An image taken at a distance; the affected area is the head or neck:
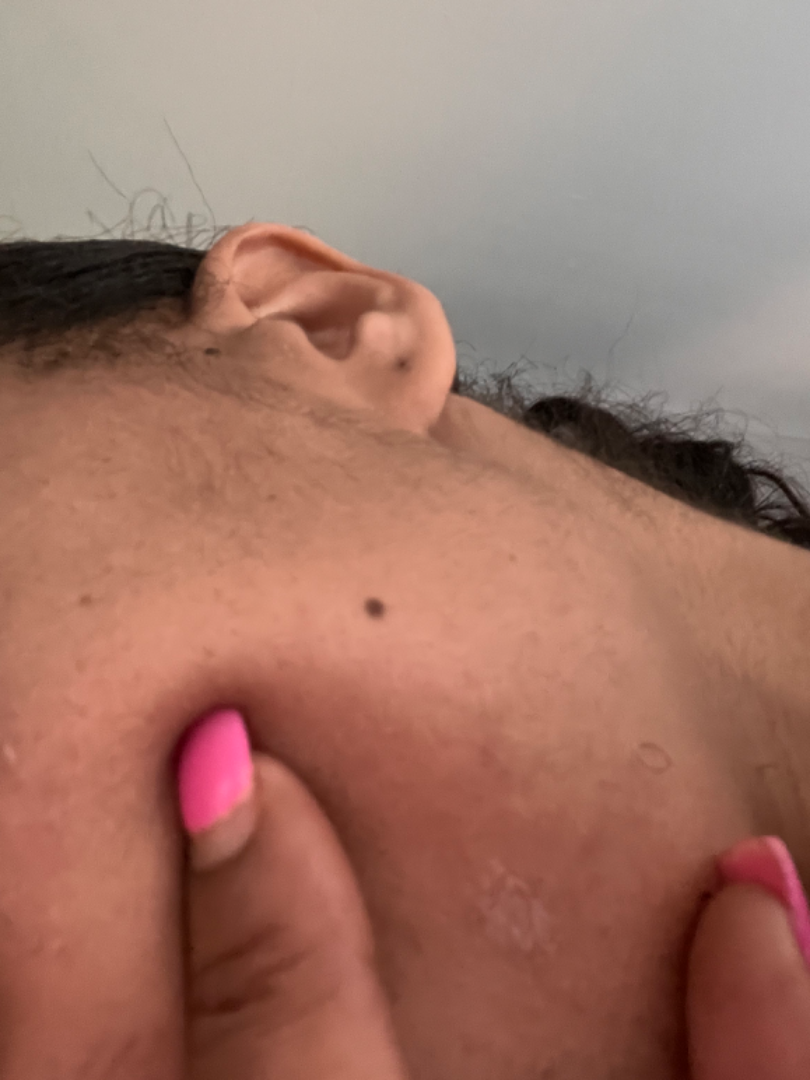dermatologist impression: the favored diagnosis is Tinea; the differential also includes Impetigo; with consideration of Herpes Simplex